The arm and leg are involved. The subject is 40–49, female. The photo was captured at a distance.
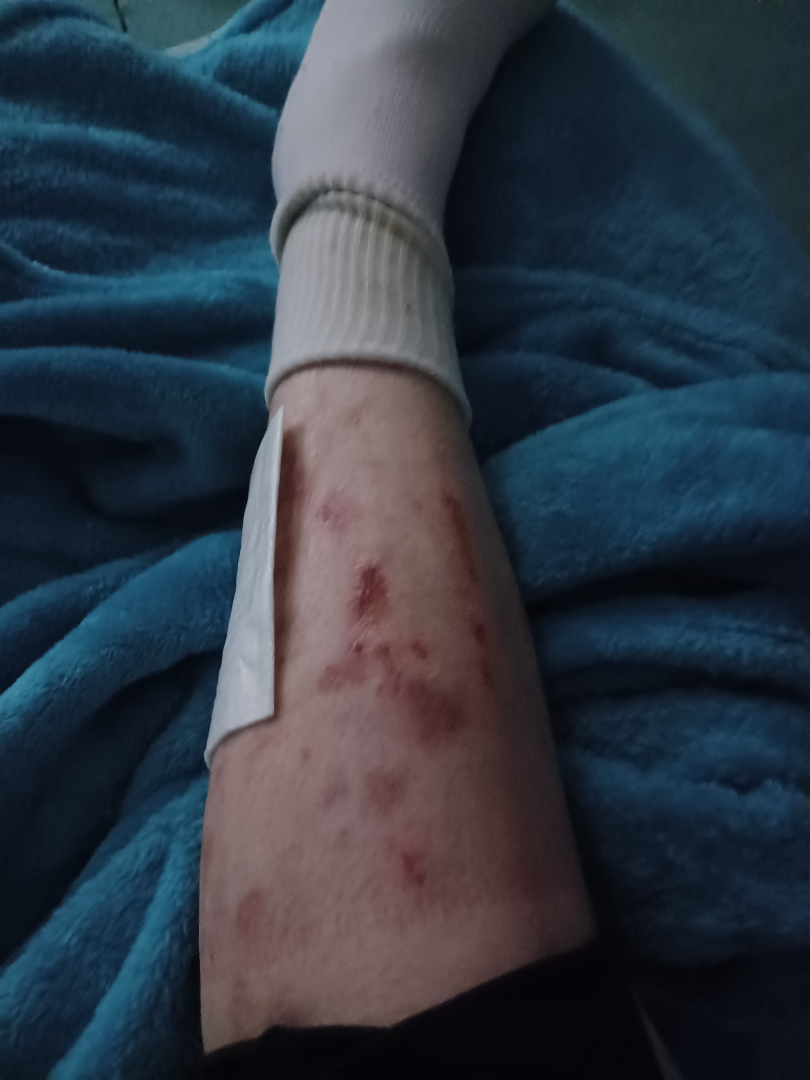Clinical context: Fitzpatrick phototype III. The patient indicates the lesion is fluid-filled, raised or bumpy and rough or flaky. The patient described the issue as a rash. Assessment: On photographic review, the impression was split between Abrasion, scrape, or scab and Bullous Pemphigoid; a more distant consideration is ecchymoses; less likely is Eczema.